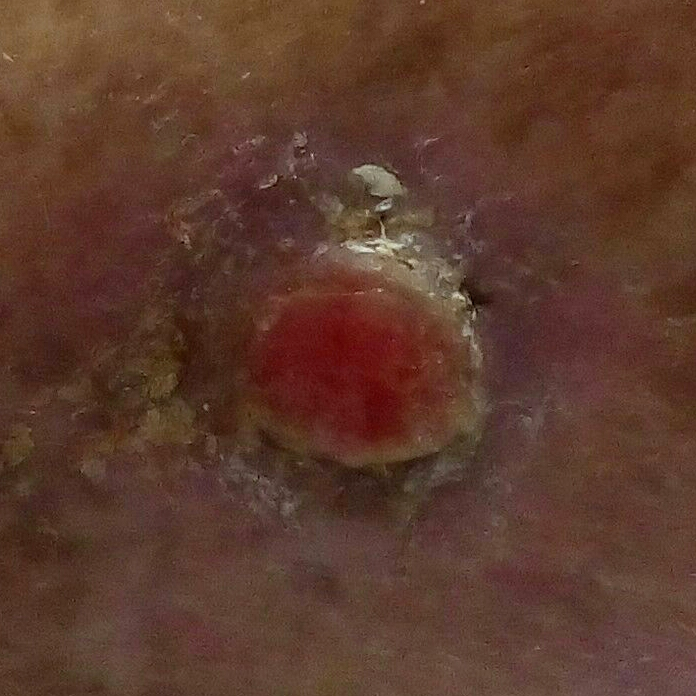A clinical photograph of a skin lesion.
A female patient aged 85.
Located on a thigh.
The patient reports that the lesion itches, is elevated, has bled, and hurts.
On biopsy, the diagnosis was a basal cell carcinoma.